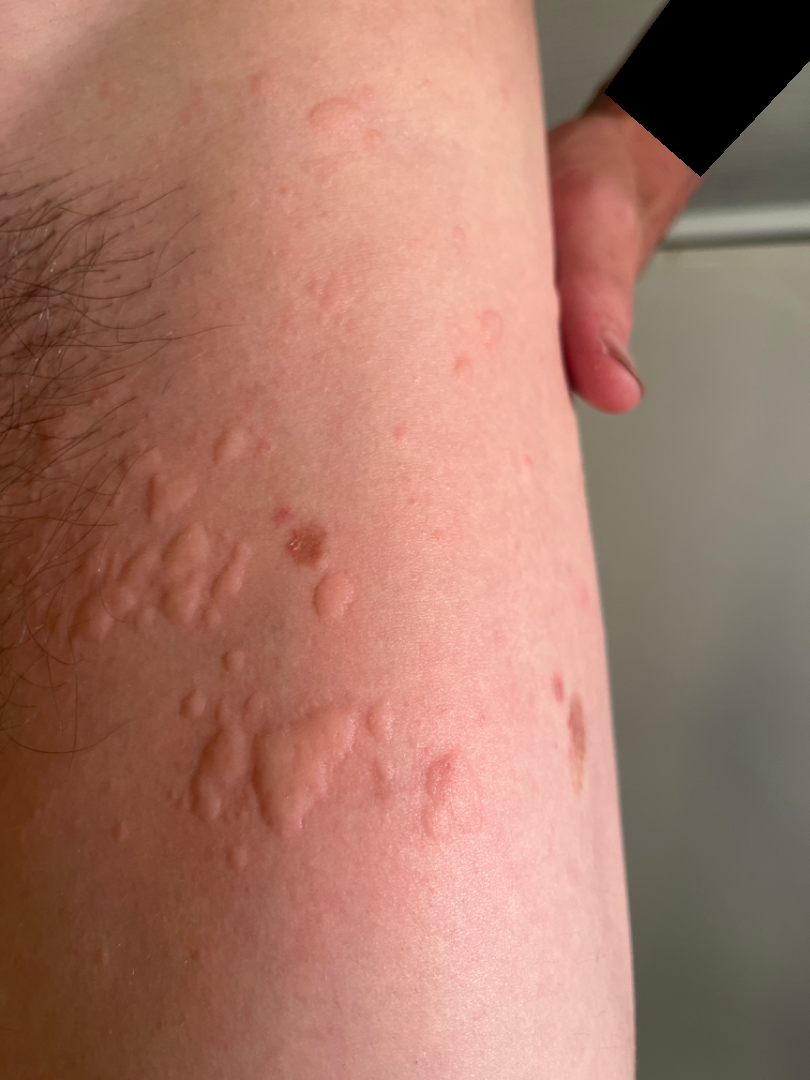Findings:
• view — at a distance
• differential — the impression is Urticaria